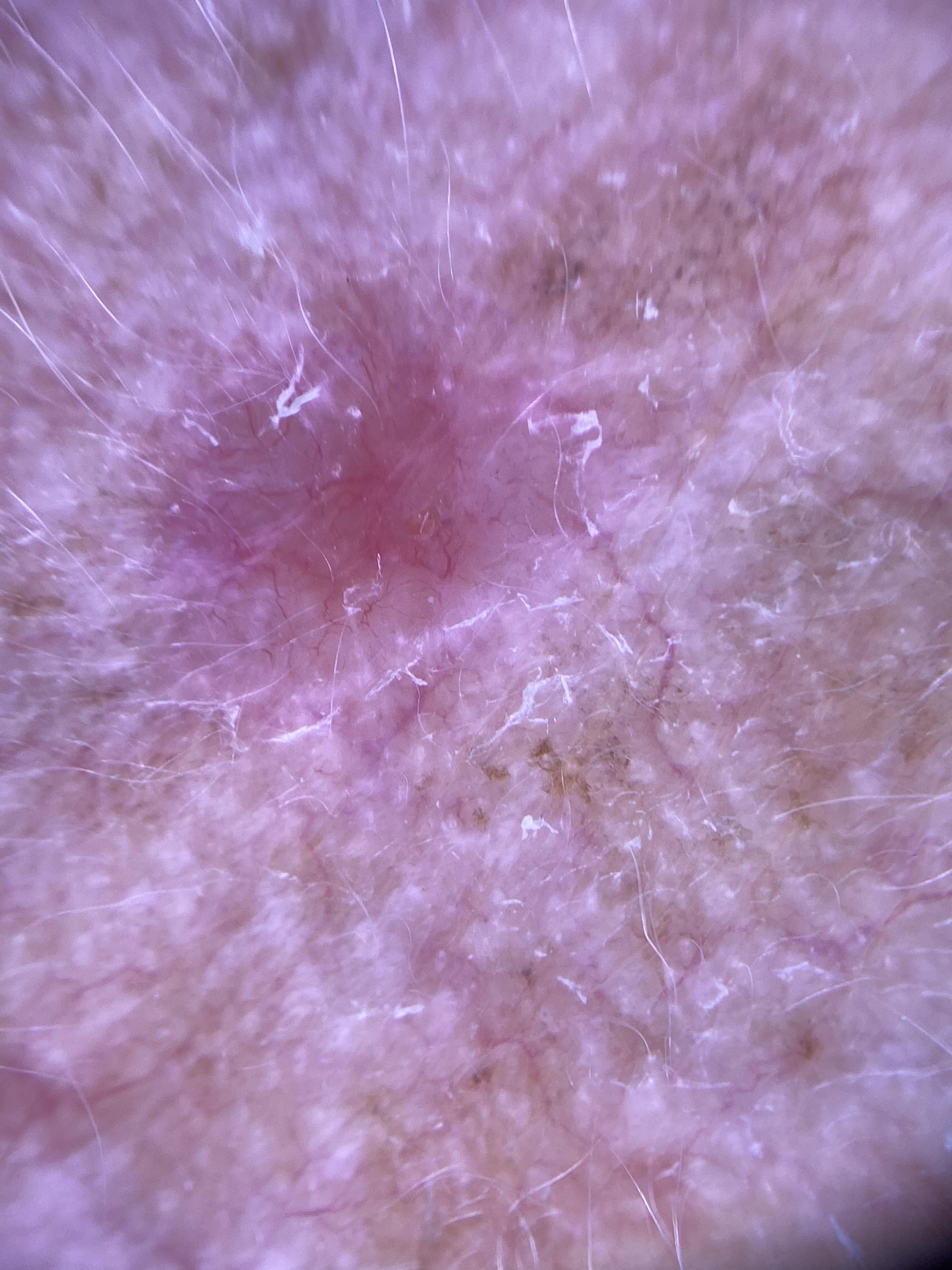The lesion was found on the head or neck.
The biopsy diagnosis was a basal cell carcinoma.